This image was taken at an angle, located on the front of the torso: 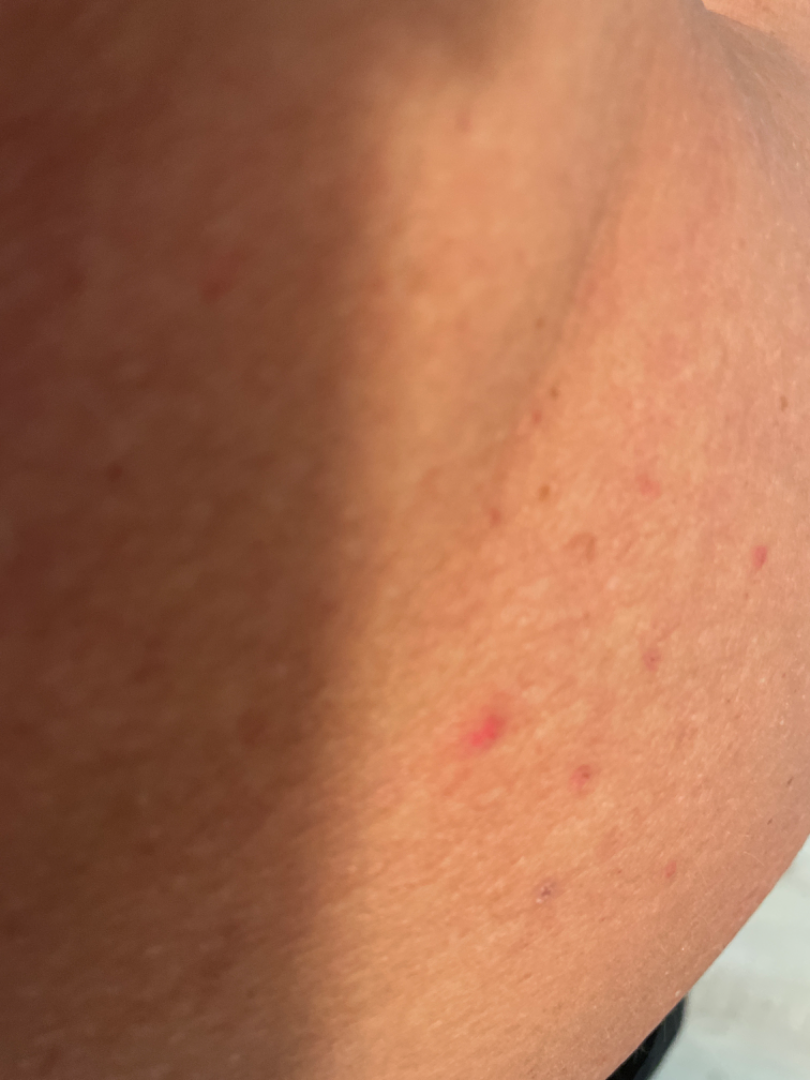{"assessment": "ungradable on photographic review", "texture": ["fluid-filled", "rough or flaky", "raised or bumpy"], "duration": "about one day"}